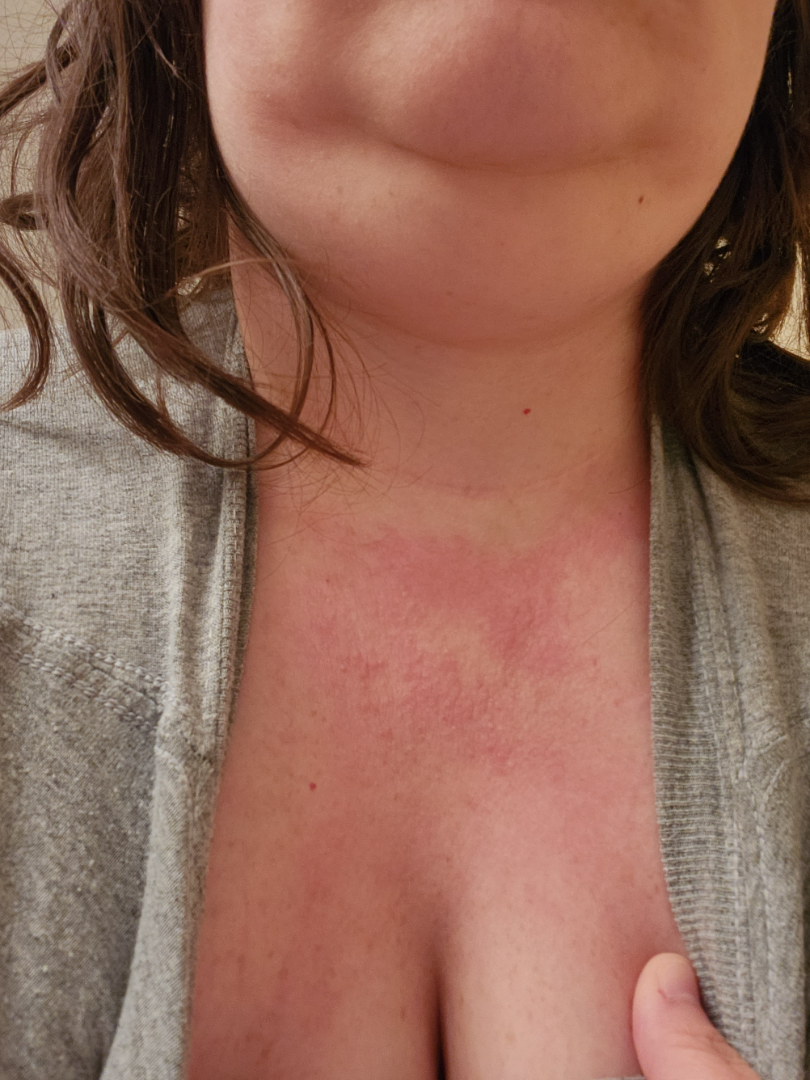{"patient": "female, age 40–49", "body_site": ["front of the torso", "head or neck"], "shot_type": "close-up", "differential": {"leading": ["Allergic Contact Dermatitis"], "considered": ["Photodermatitis"], "unlikely": ["Drug Rash", "Acute dermatitis, NOS", "Rosacea"]}}